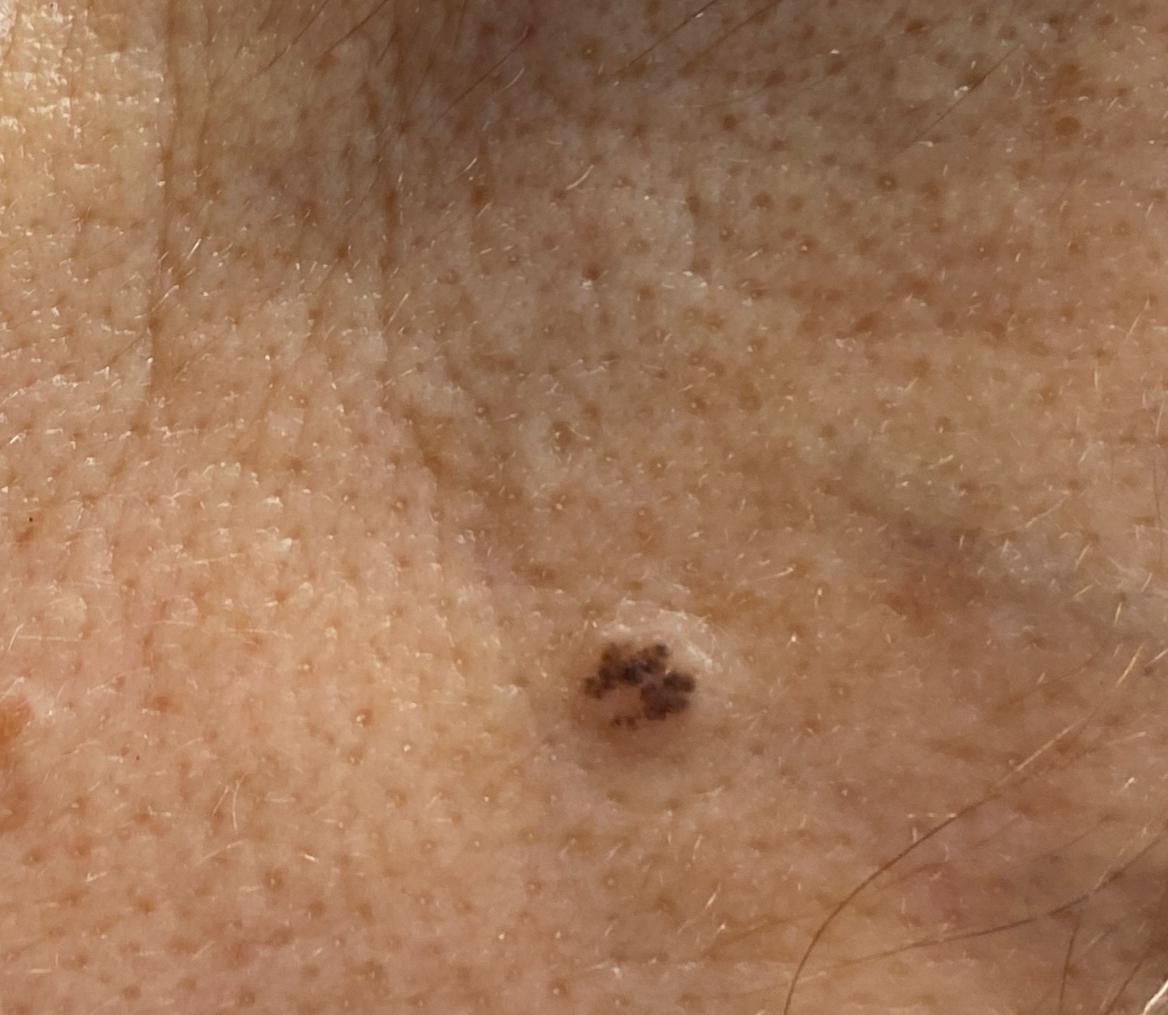<skin_lesion>
<image>clinical overview photograph</image>
<lesion_location>
<region>the head or neck</region>
</lesion_location>
<diagnosis>
<name>Basal cell carcinoma</name>
<malignancy>malignant</malignancy>
<confirmation>histopathology</confirmation>
<lineage>adnexal</lineage>
</diagnosis>
</skin_lesion>